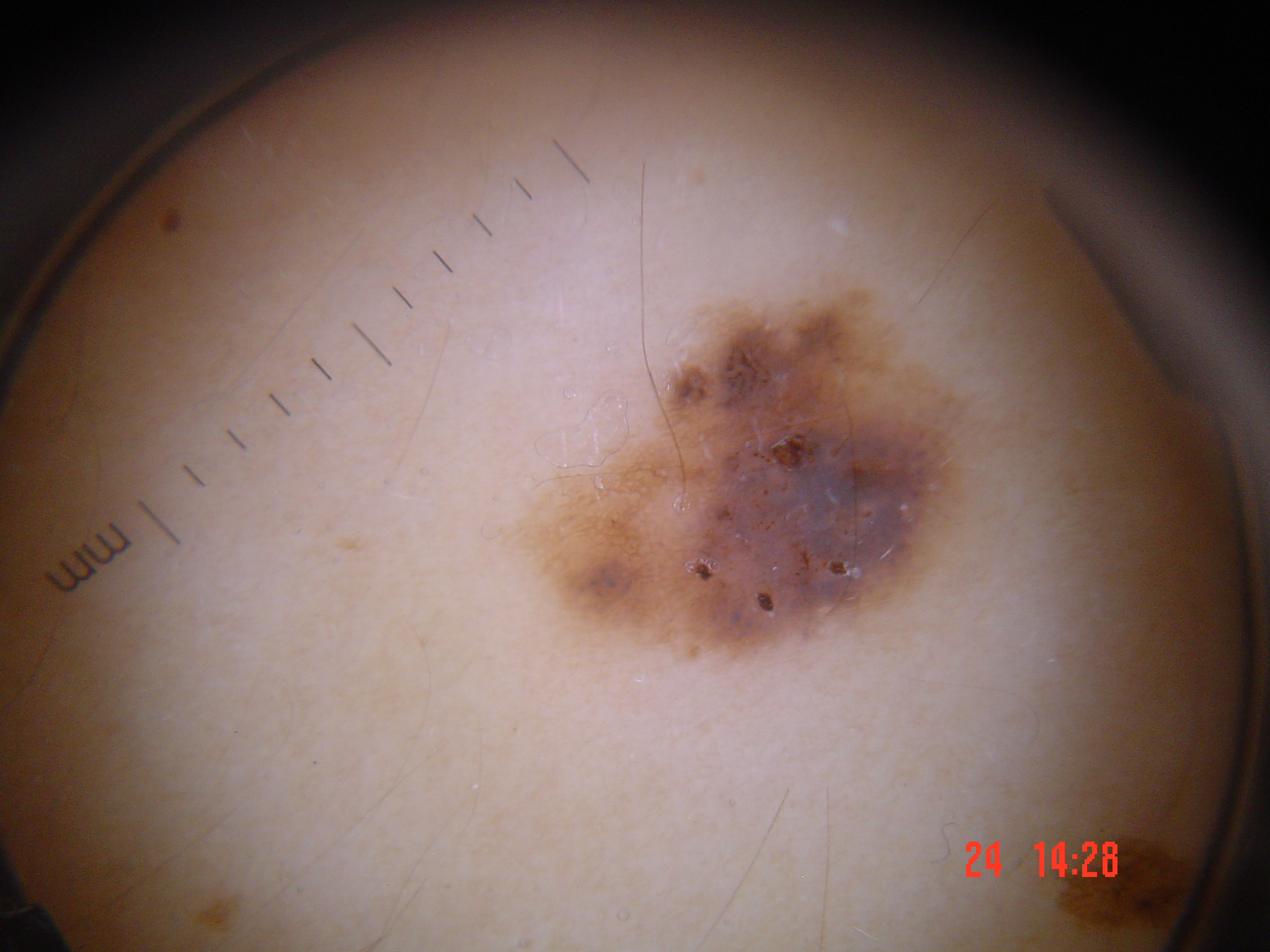Case:
* imaging · dermatoscopy
* label · congenital compound nevus (expert consensus)